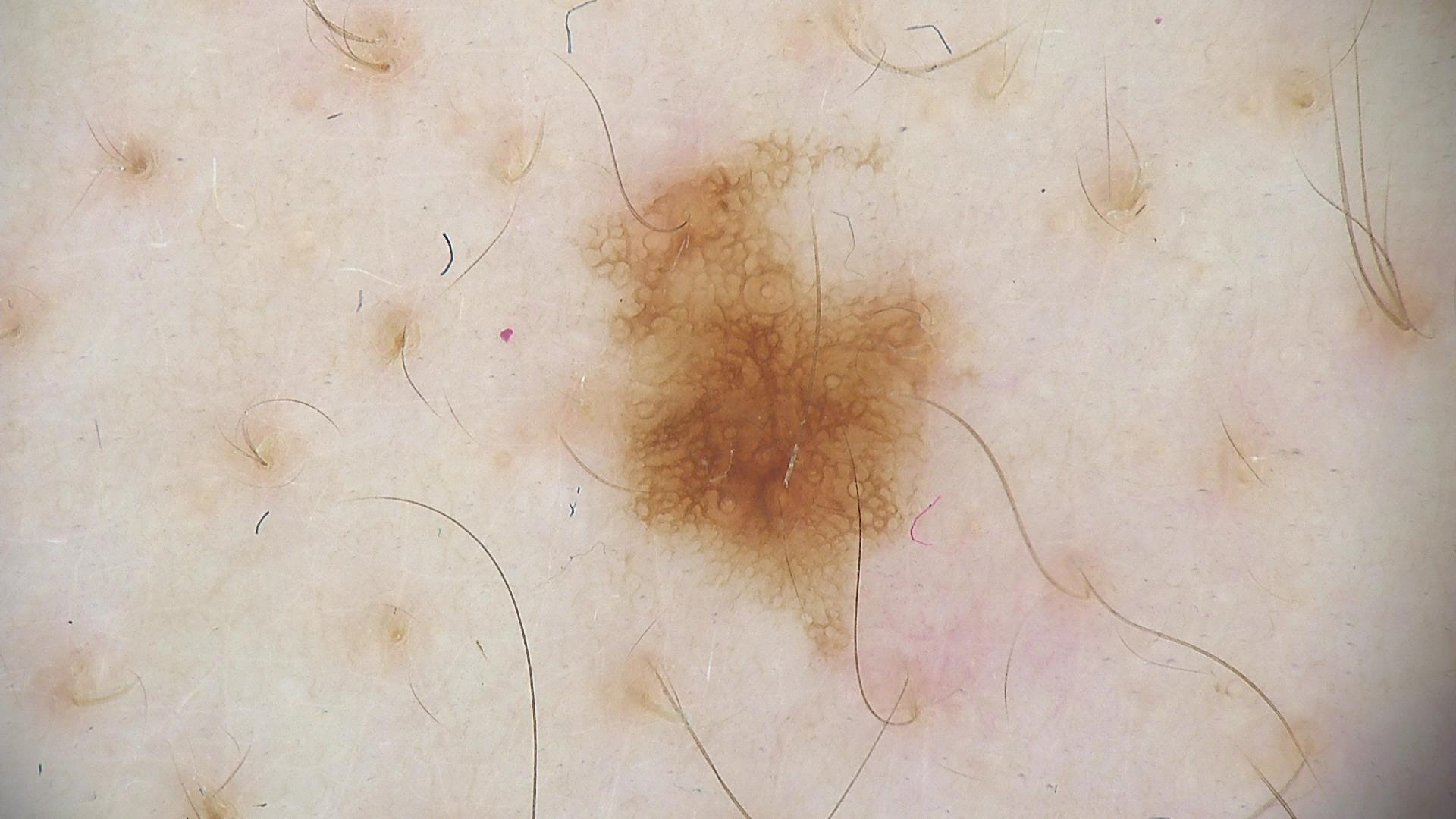Dermoscopy of a skin lesion. Consistent with a benign lesion — a dysplastic junctional nevus.